This is a close-up image — 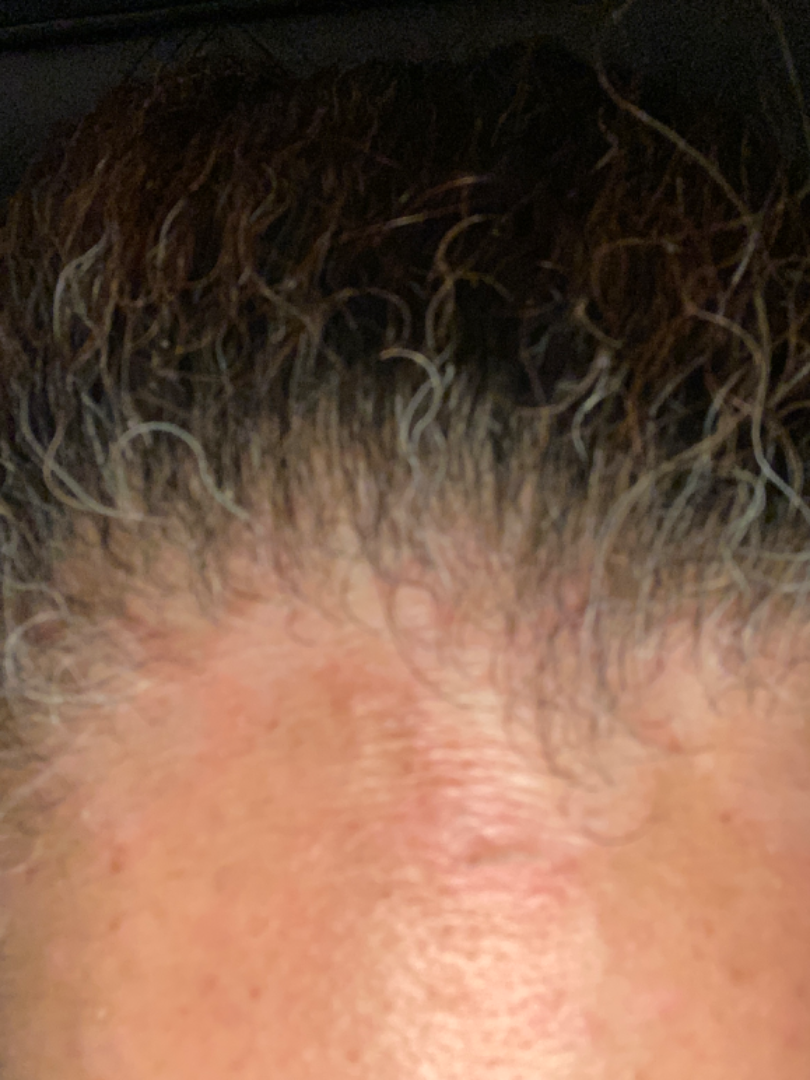The reviewing dermatologist was unable to assign a differential diagnosis from the image.